The contributor notes itching. The contributor notes the lesion is raised or bumpy. Fitzpatrick IV; lay graders estimated Monk Skin Tone 4 (US pool) or 2 (India pool). Close-up view. The affected area is the front of the torso and leg. The condition has been present for less than one week.
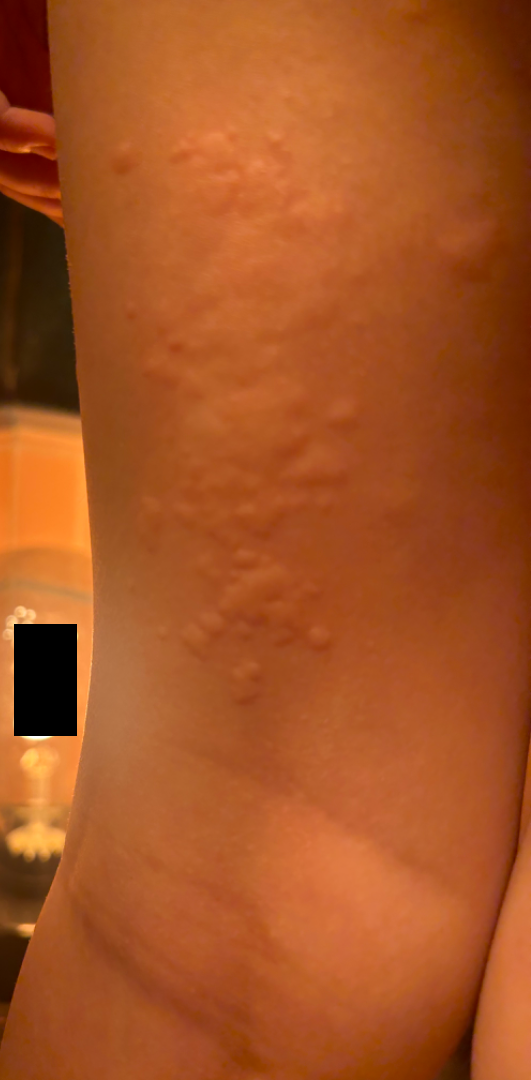On remote review of the image, most likely Urticaria; also consider Allergic Contact Dermatitis; a more distant consideration is Insect Bite.